The affected area is the leg and arm · skin tone: Fitzpatrick III; lay graders estimated MST 2–3 · texture is reported as raised or bumpy · the photograph was taken at a distance · reported duration is less than one week — 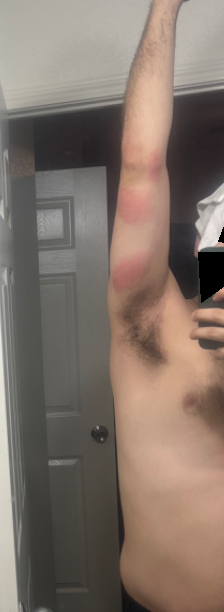Most consistent with Insect Bite.